Dermoscopy of a skin lesion — 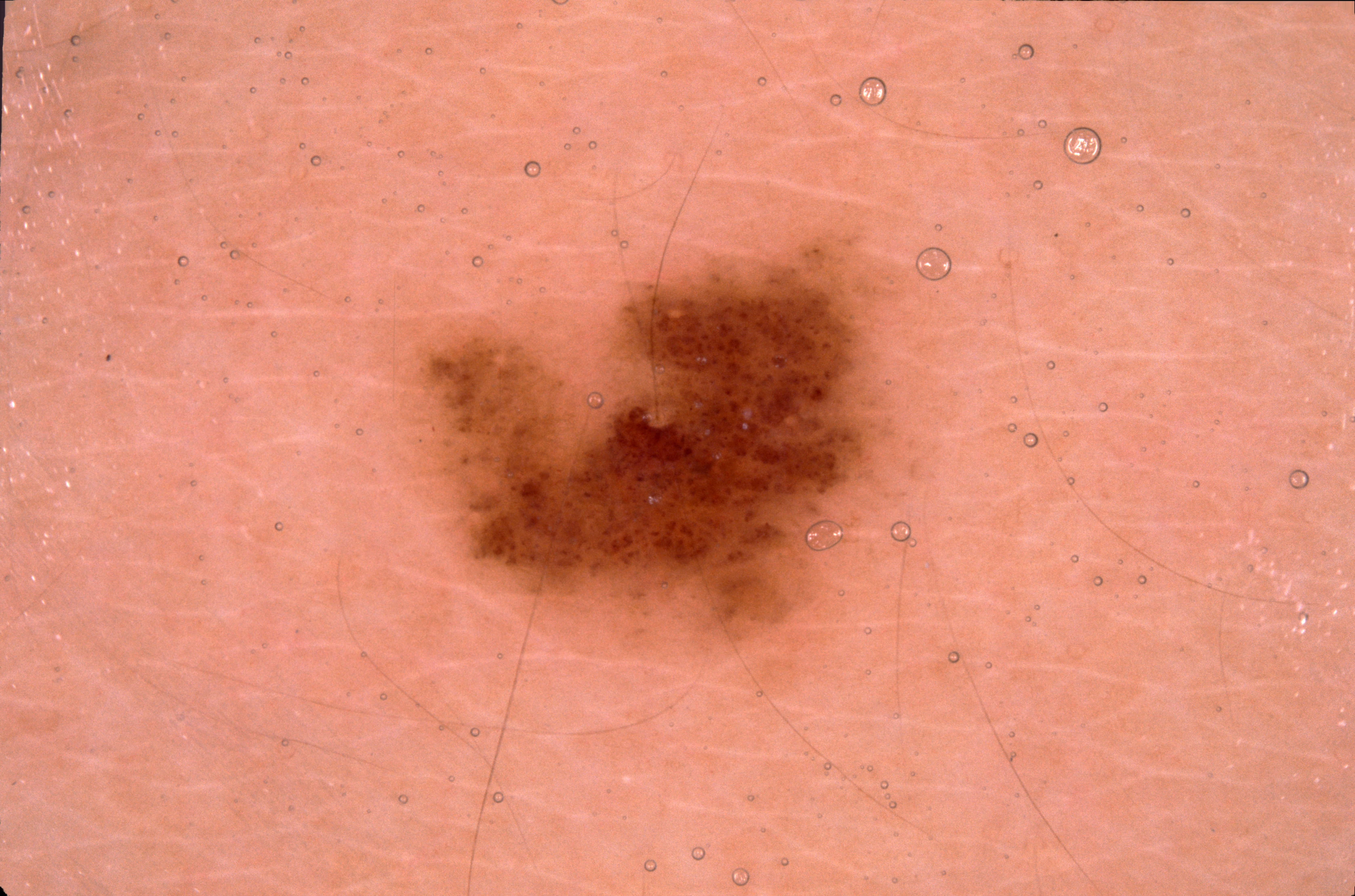Summary:
Dermoscopic examination shows no streaks, negative network, pigment network, or milia-like cysts. As (left, top, right, bottom), the visible lesion spans bbox=[415, 236, 896, 653].
Assessment:
The clinical diagnosis was a melanocytic nevus.